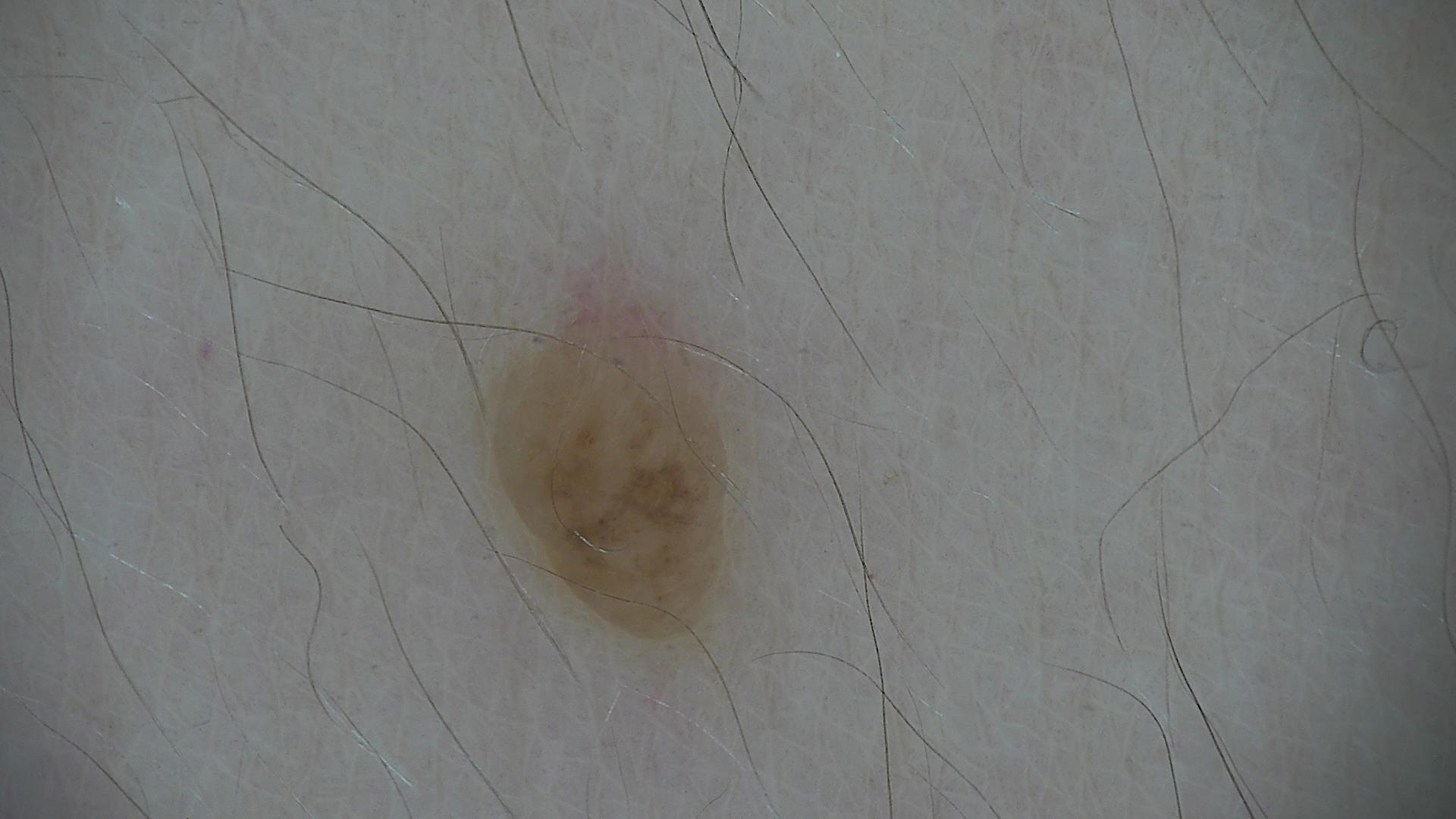Classified as a dermal nevus.